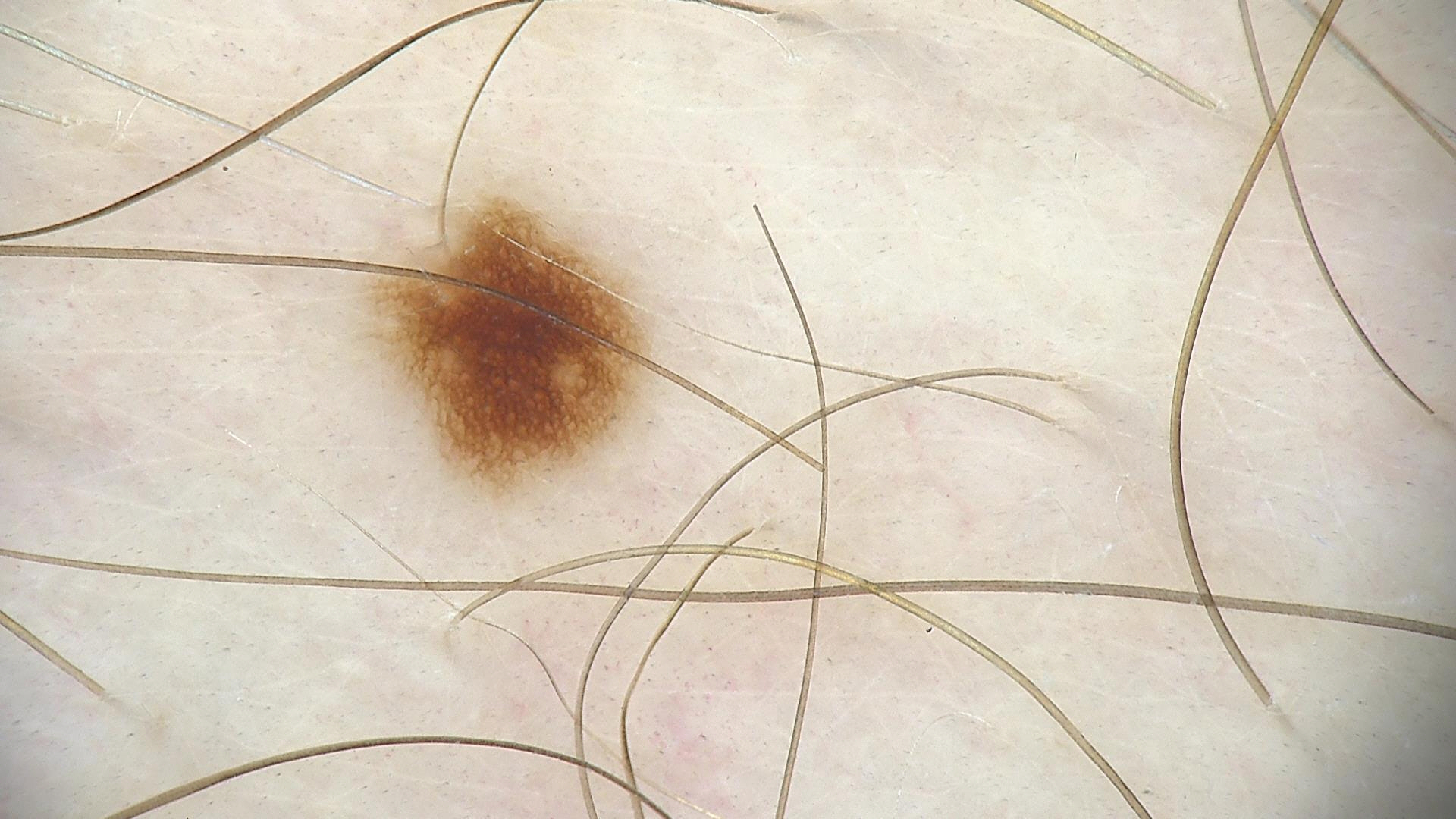imaging=dermoscopy
assessment=dysplastic junctional nevus (expert consensus)